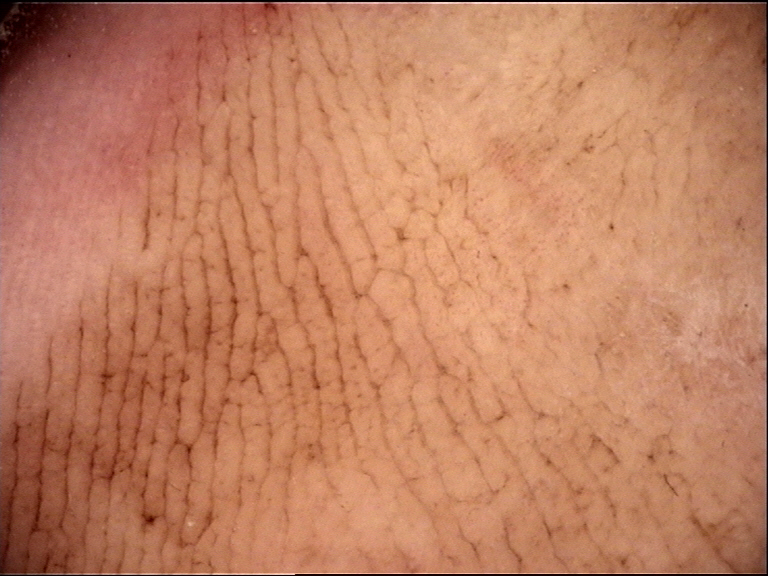<case>
  <diagnosis>
    <name>acral junctional nevus</name>
    <code>ajb</code>
    <malignancy>benign</malignancy>
    <super_class>melanocytic</super_class>
    <confirmation>expert consensus</confirmation>
  </diagnosis>
</case>